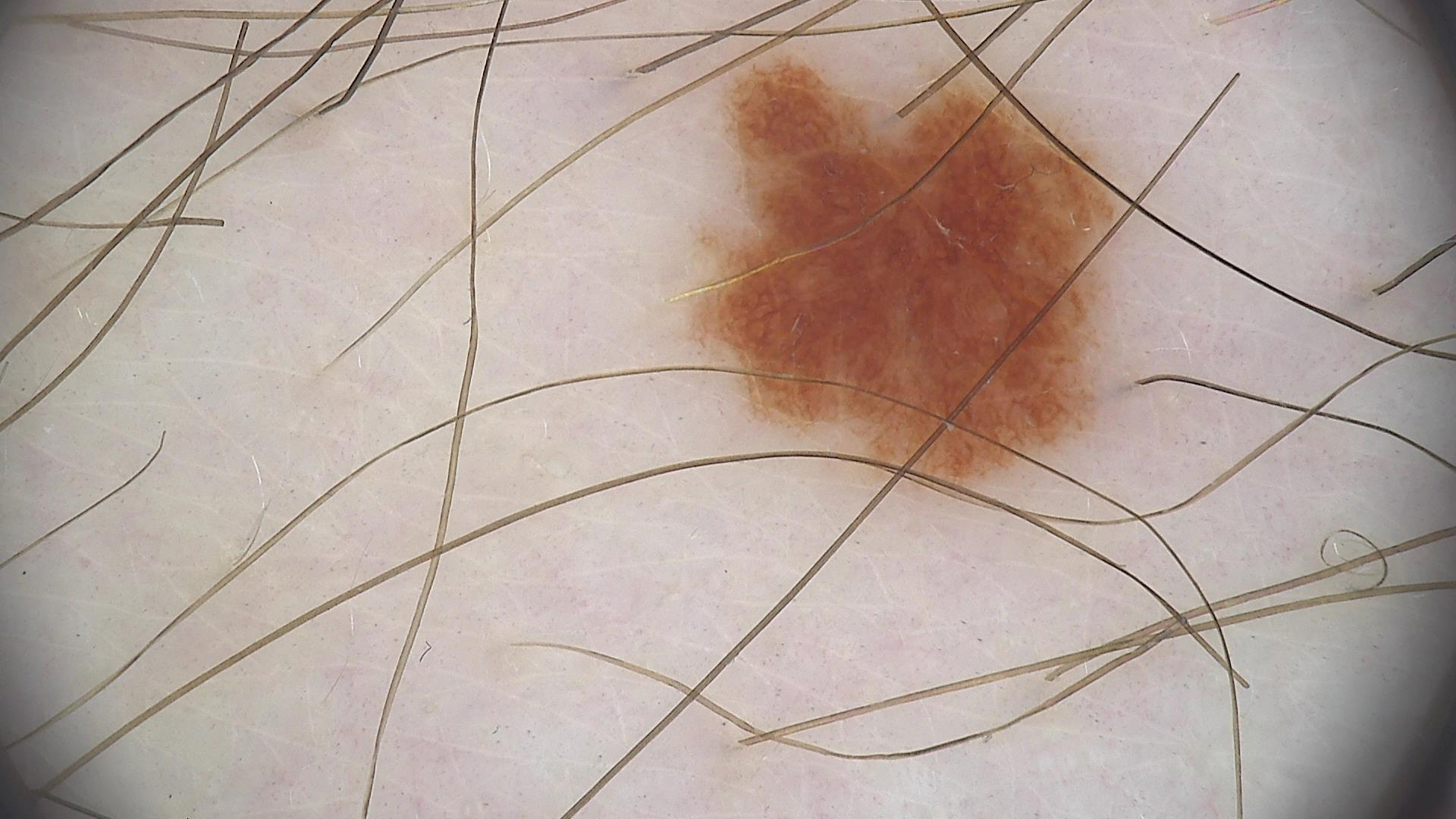Diagnosed as a dysplastic junctional nevus.